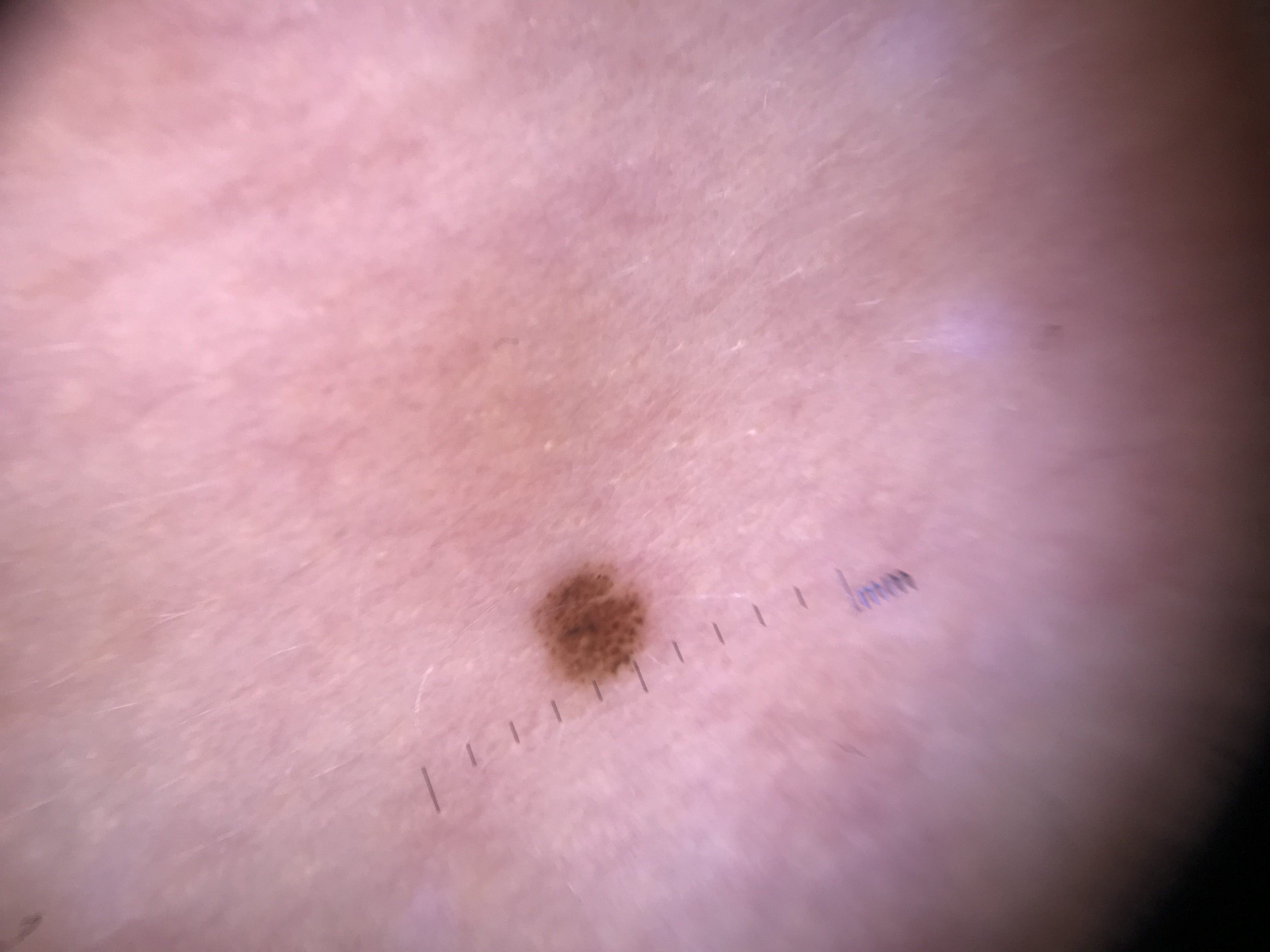The diagnostic label was a junctional nevus.